The photo was captured at a distance; the affected area is the arm, head or neck, front of the torso and back of the hand — 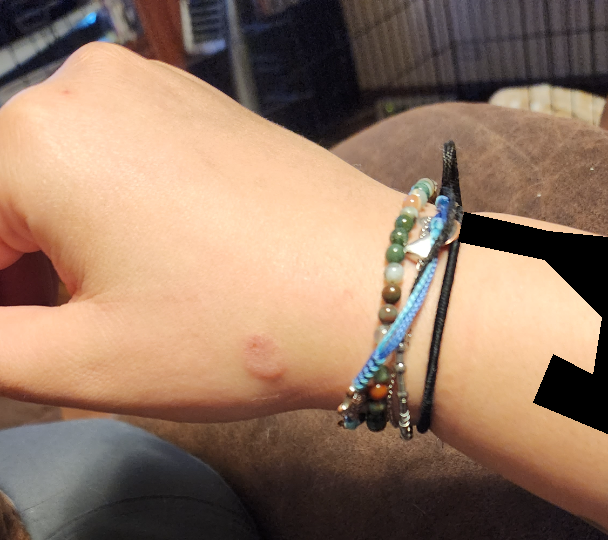Reported lesion symptoms include itching and pain. Skin tone: FST III; human graders estimated a Monk Skin Tone of 3. The patient described the issue as a rash. The patient reports the condition has been present for less than one week. Associated systemic symptoms include fatigue. The lesion is described as flat, raised or bumpy and rough or flaky. On independent review by the dermatologists: most likely Eczema; an alternative is Tinea; lower on the differential is Impetigo; a remote consideration is Allergic Contact Dermatitis.